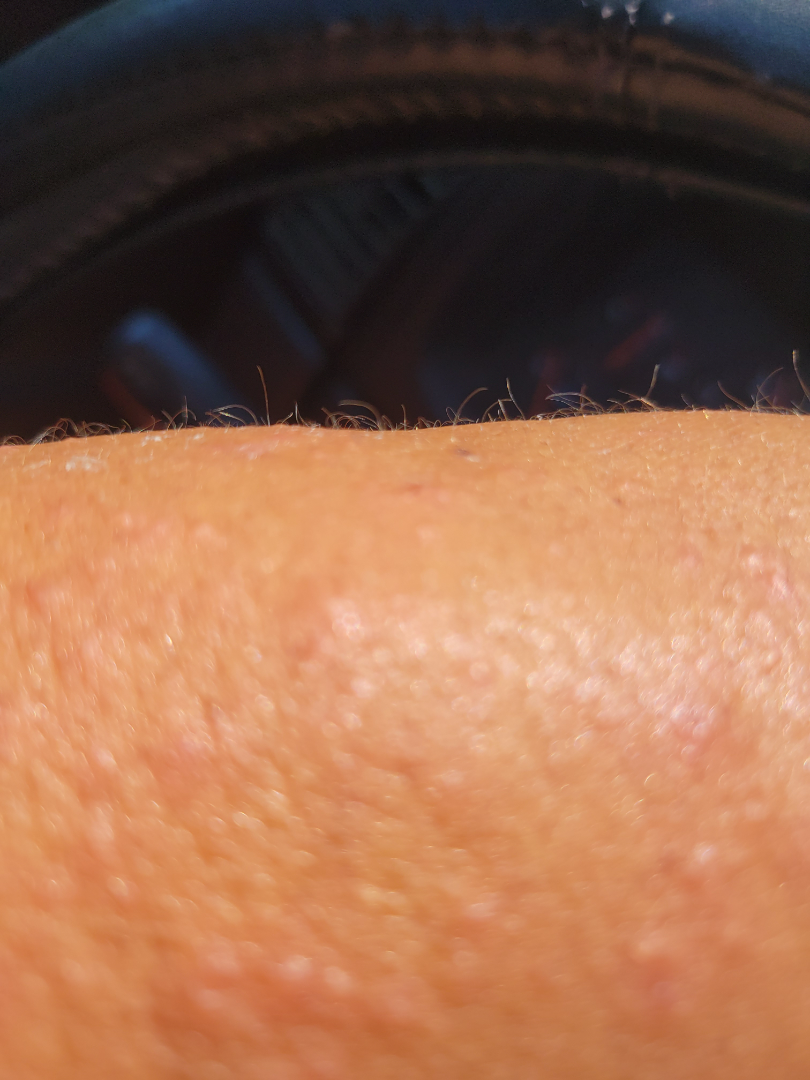The case was indeterminate on photographic review. This is a close-up image. The arm is involved.